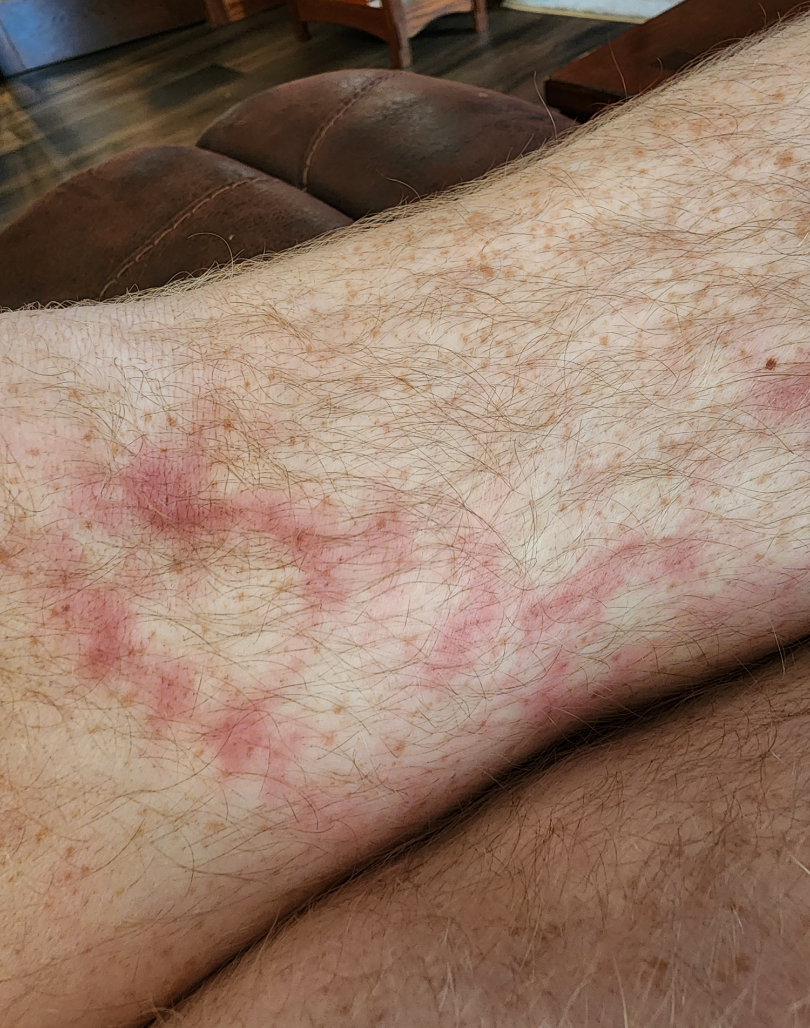Q: What is the framing?
A: close-up
Q: What is the differential diagnosis?
A: the impression was split between Livedo reticularis and Erythema ab igne